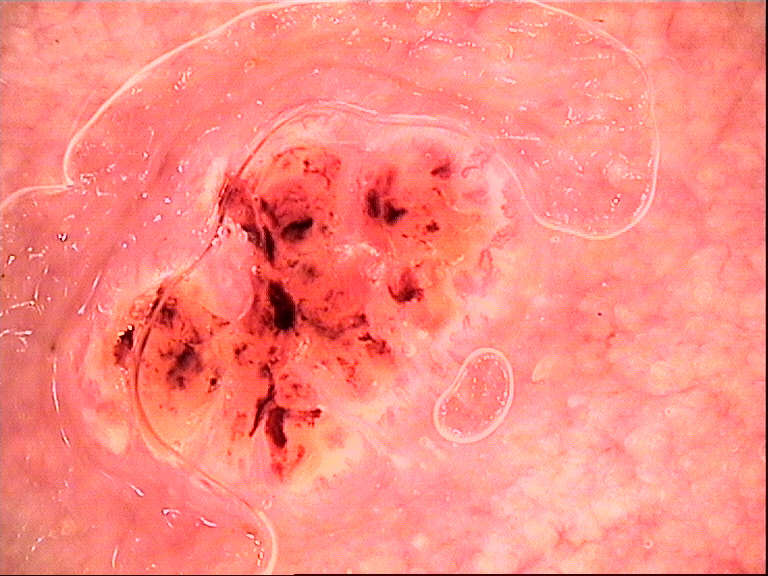label=squamous cell carcinoma (biopsy-proven).